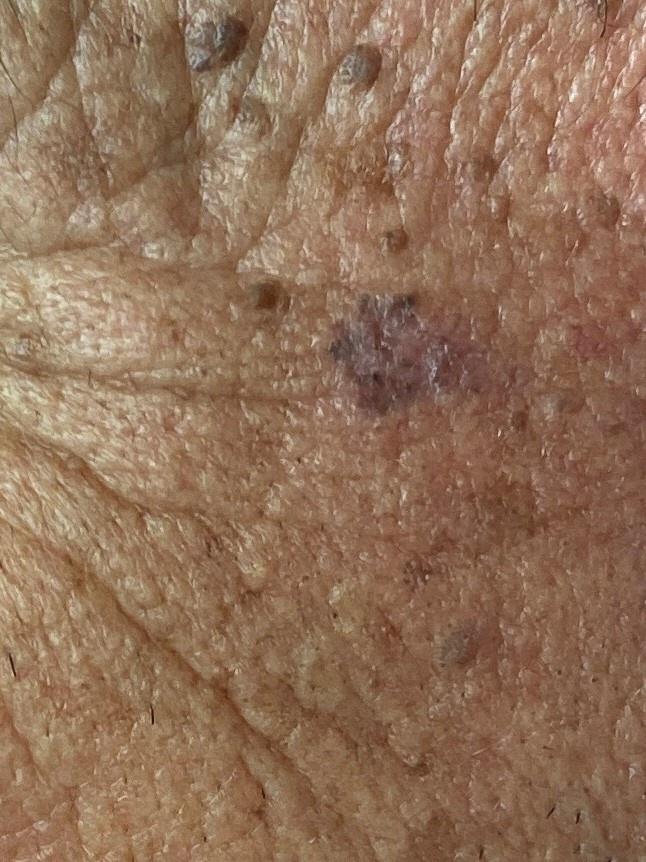A clinical photograph showing a skin lesion in context.
A male subject aged 83 or over.
The lesion involves the head or neck.
Histopathological examination showed a basal cell carcinoma.